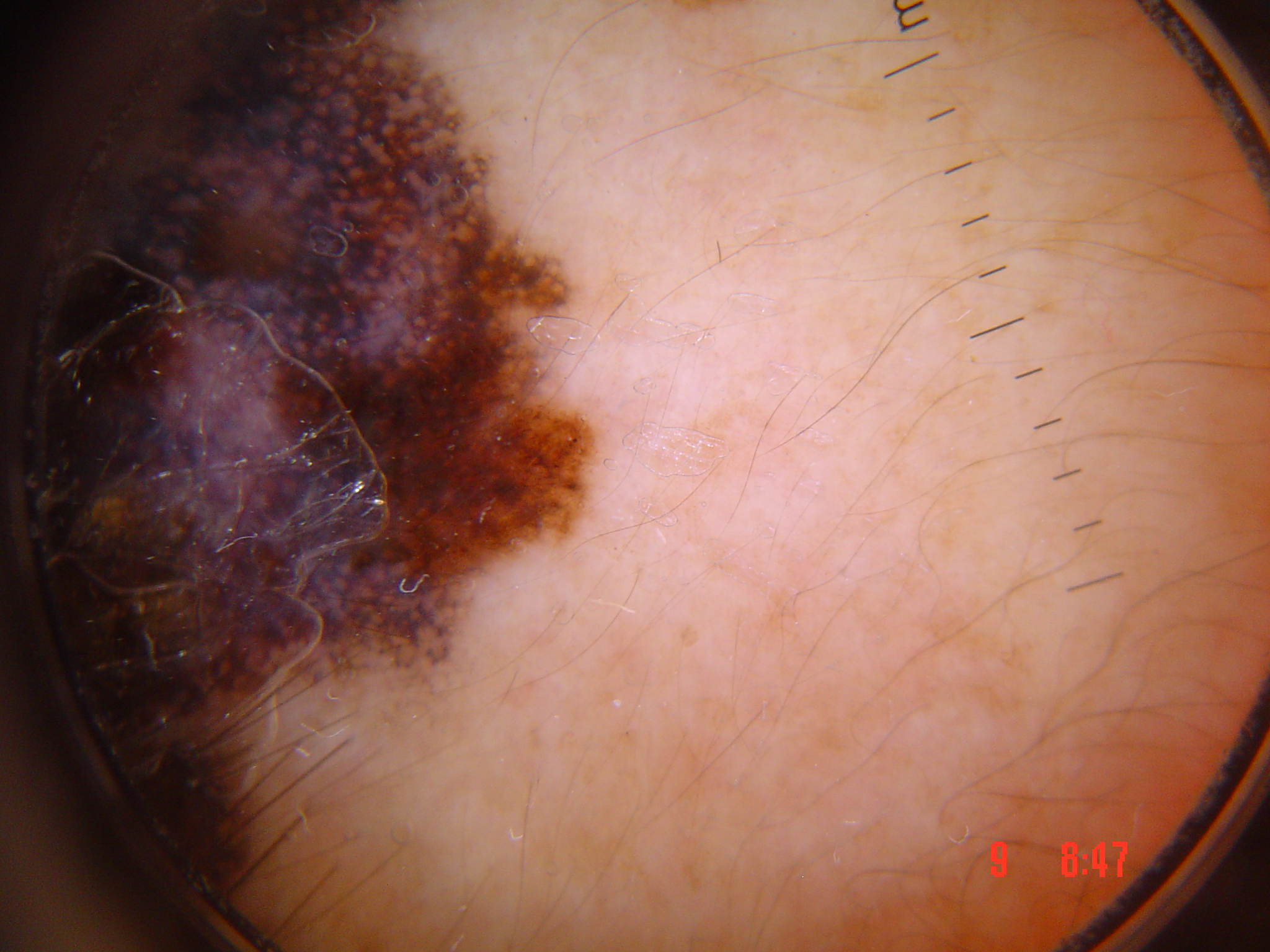pathology: lentigo maligna (biopsy-proven).